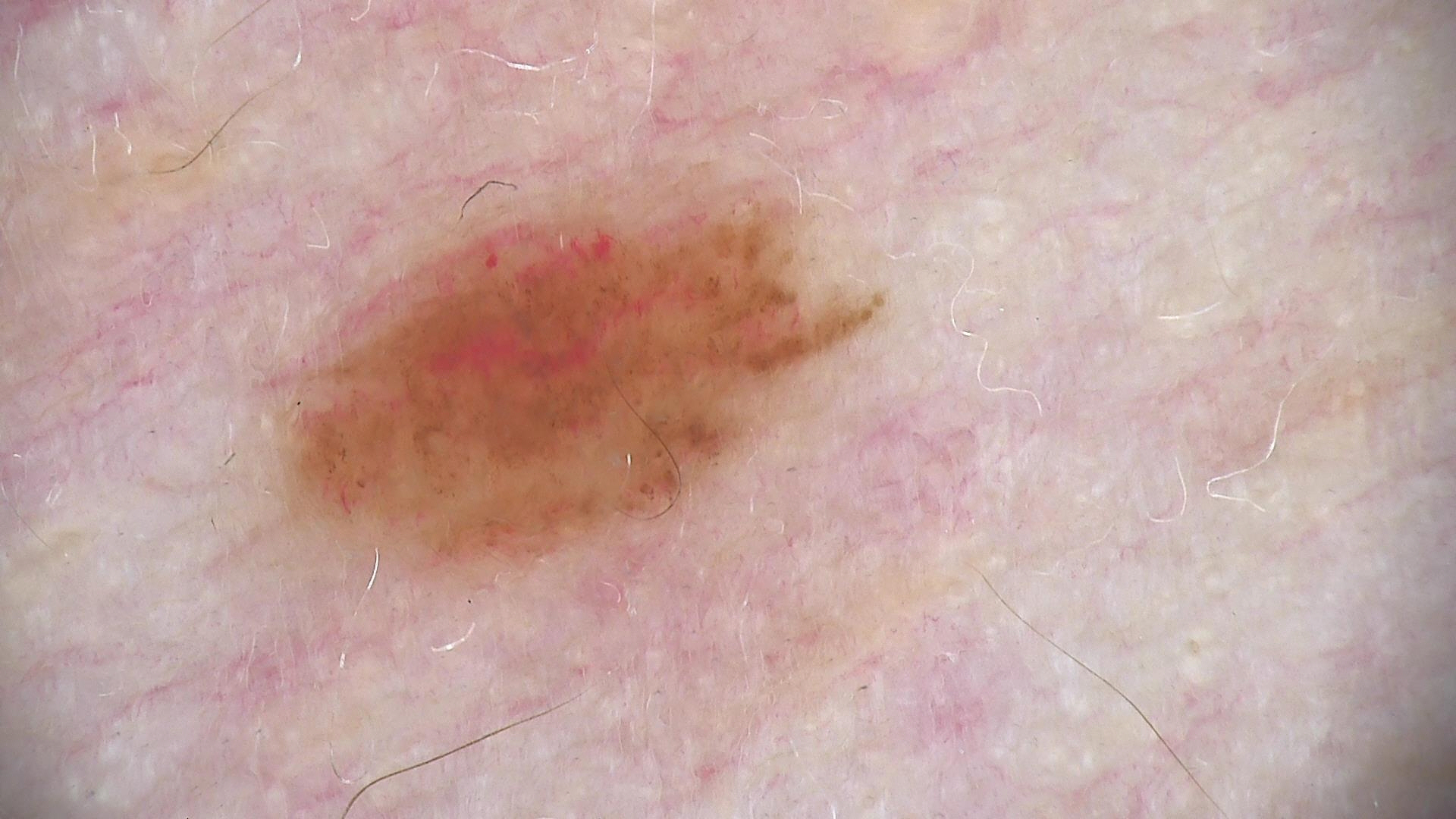Diagnosed as a benign lesion — a dysplastic junctional nevus.